A dermoscopic image of a skin lesion.
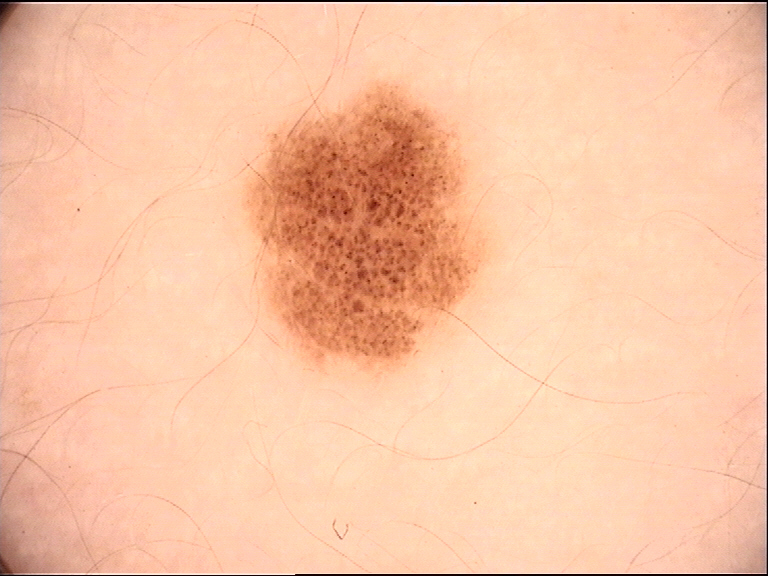label = compound nevus (expert consensus).